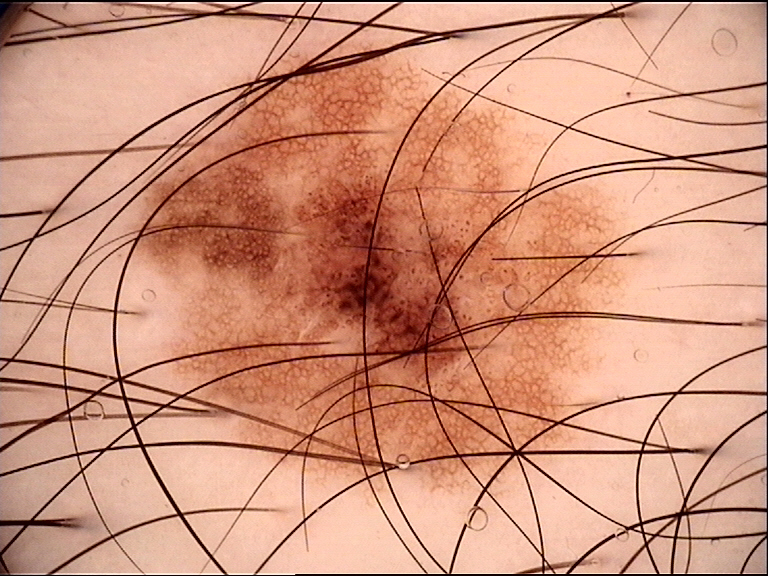Impression:
Classified as a dysplastic junctional nevus.